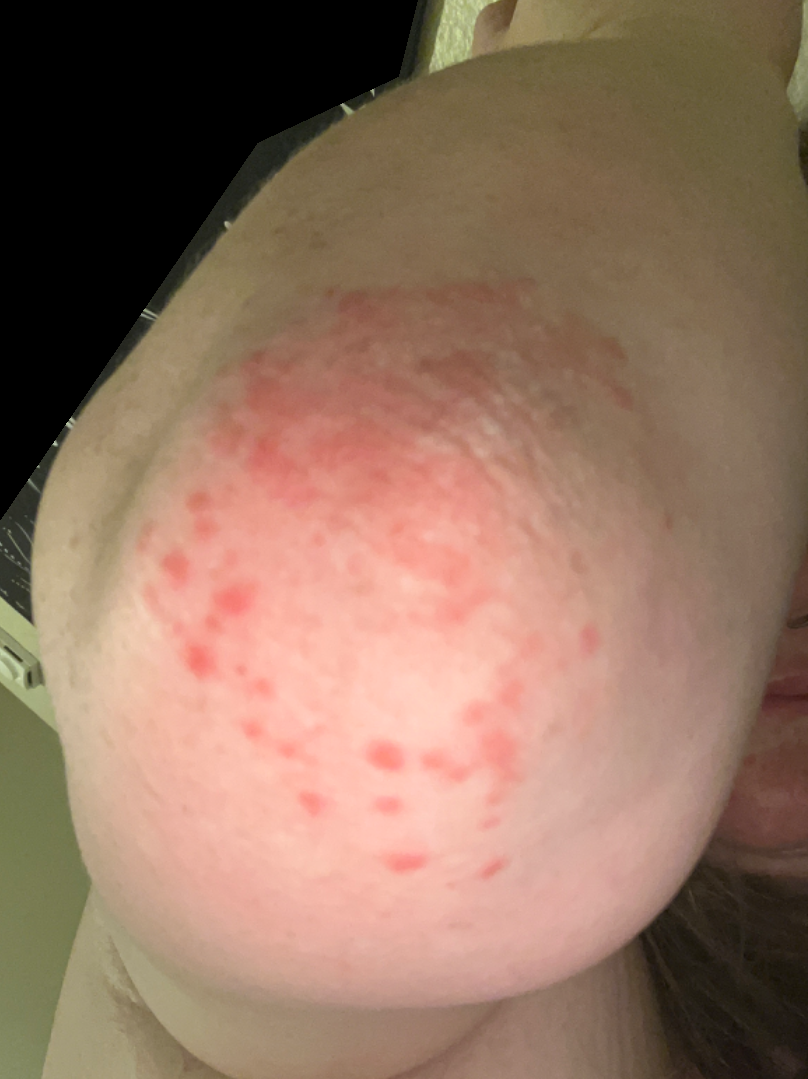The subject is 18–29, female.
A close-up photograph.
The back of the hand is involved.
On teledermatology review, the leading impression is Psoriasis; less likely is Dermatitis herpetiformis; lower on the differential is Allergic Contact Dermatitis; less probable is Acute dermatitis, NOS; a more distant consideration is Eczema.